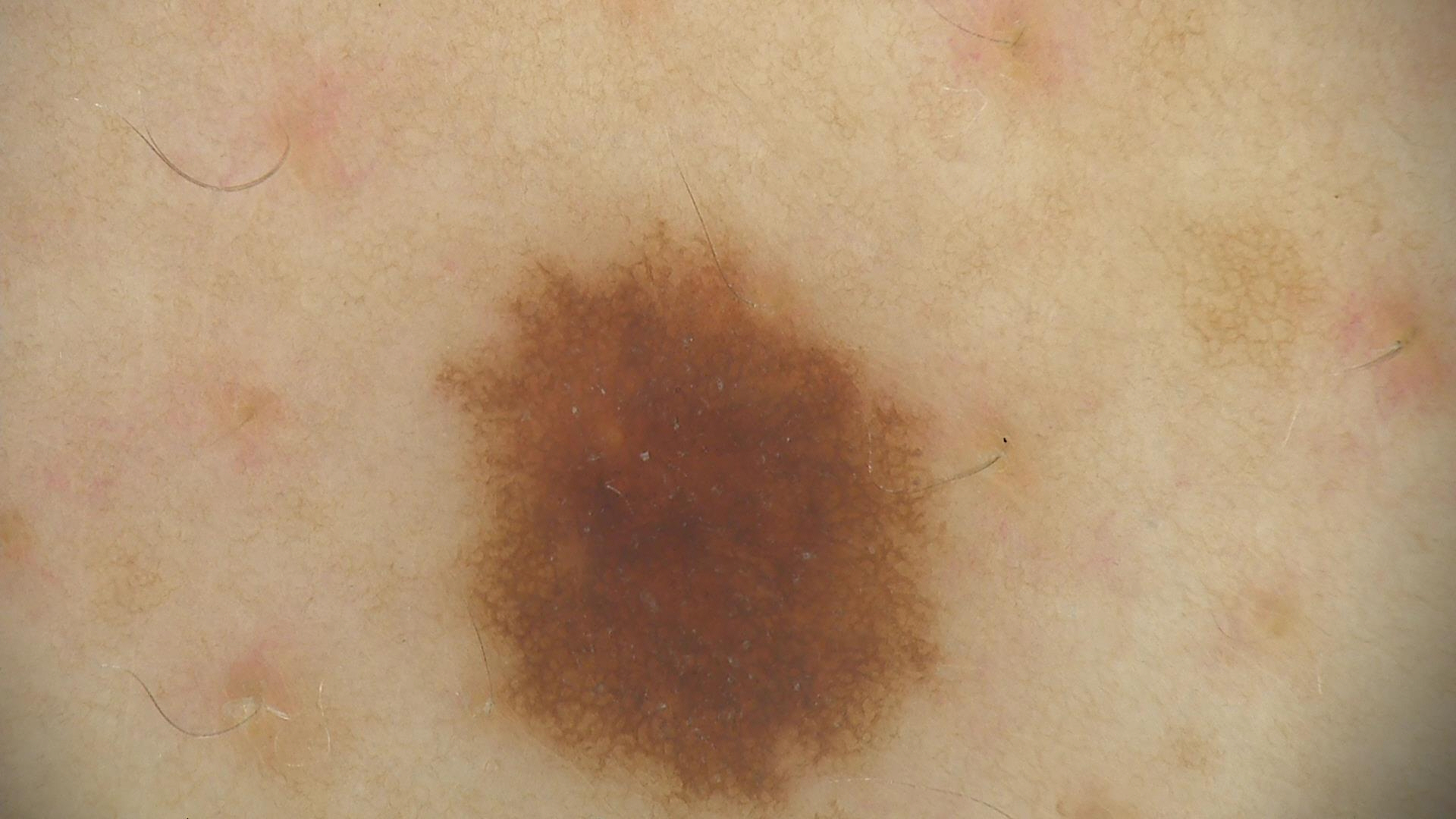Case:
A skin lesion imaged with a dermatoscope.
Impression:
Diagnosed as a dysplastic junctional nevus.